Self-categorized by the patient as a rash. The lesion is associated with bothersome appearance. No associated systemic symptoms reported. The patient is male. This image was taken at an angle. The head or neck is involved:
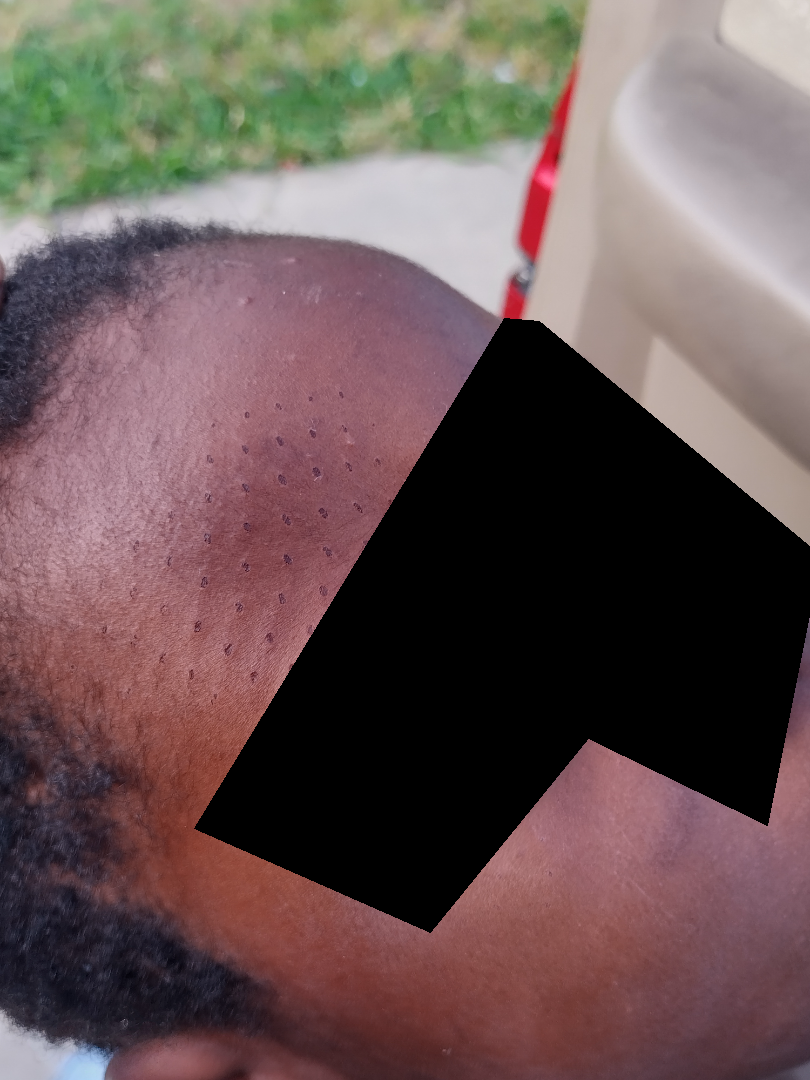Findings:
- assessment: indeterminate